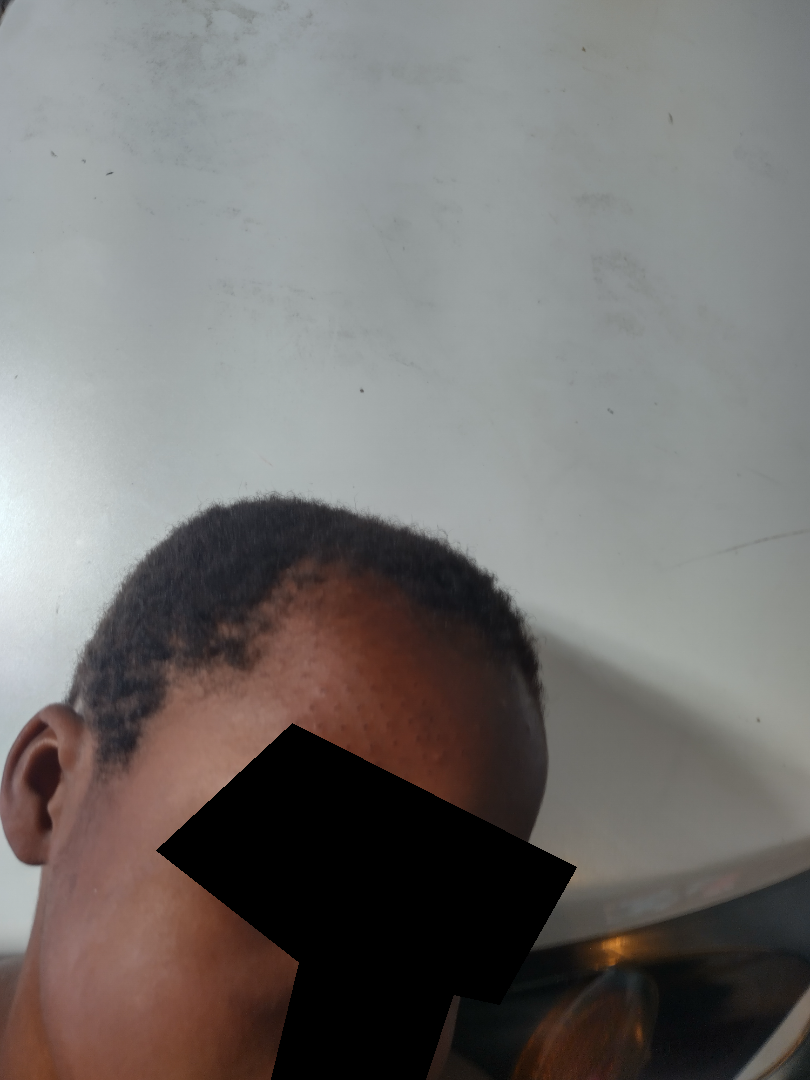| key | value |
|---|---|
| assessment | ungradable on photographic review |
| duration | about one day |
| body site | head or neck |
| reported symptoms | bothersome appearance |
| self-categorized as | a rash |
| skin tone | Fitzpatrick phototype V; non-clinician graders estimated Monk Skin Tone 5 or 7 |
| photo taken | at a distance |
| contributor | male |